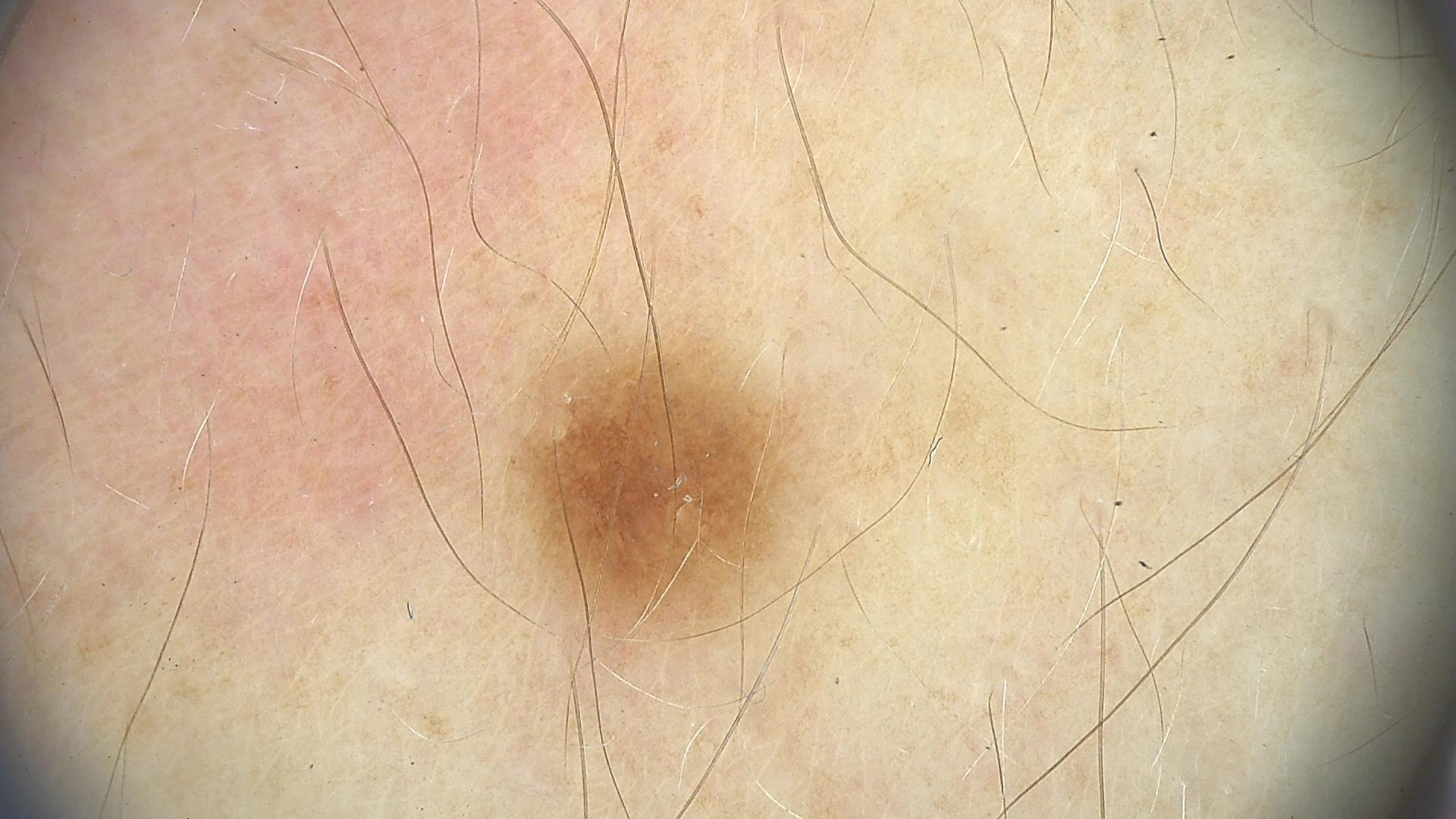A dermoscopy image of a single skin lesion. Labeled as a dysplastic junctional nevus.